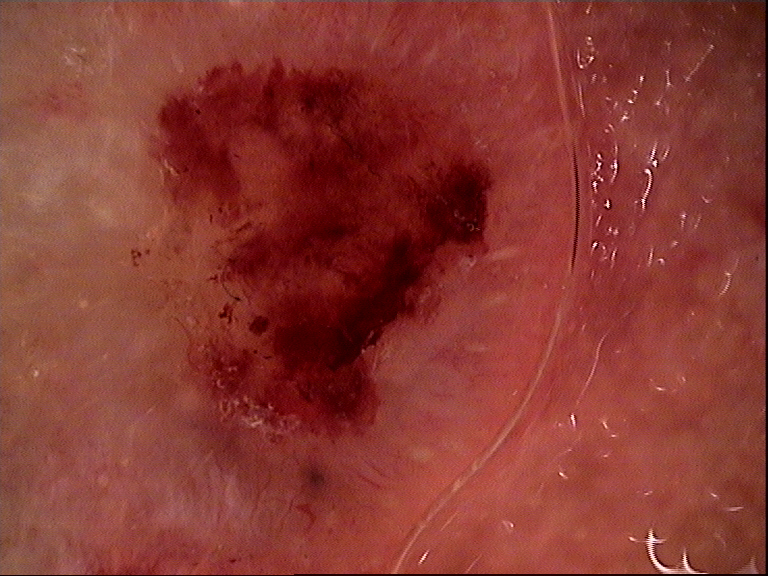label: basal cell carcinoma (biopsy-proven).